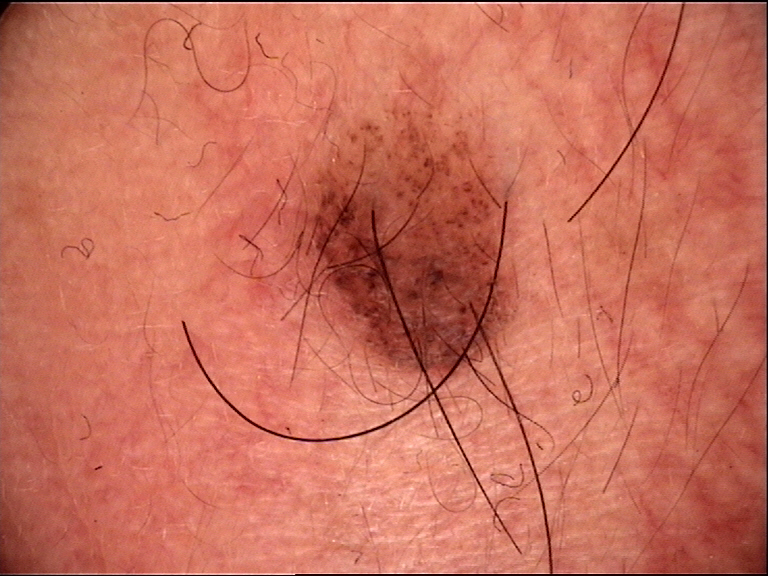Q: What is this lesion?
A: compound nevus (expert consensus)